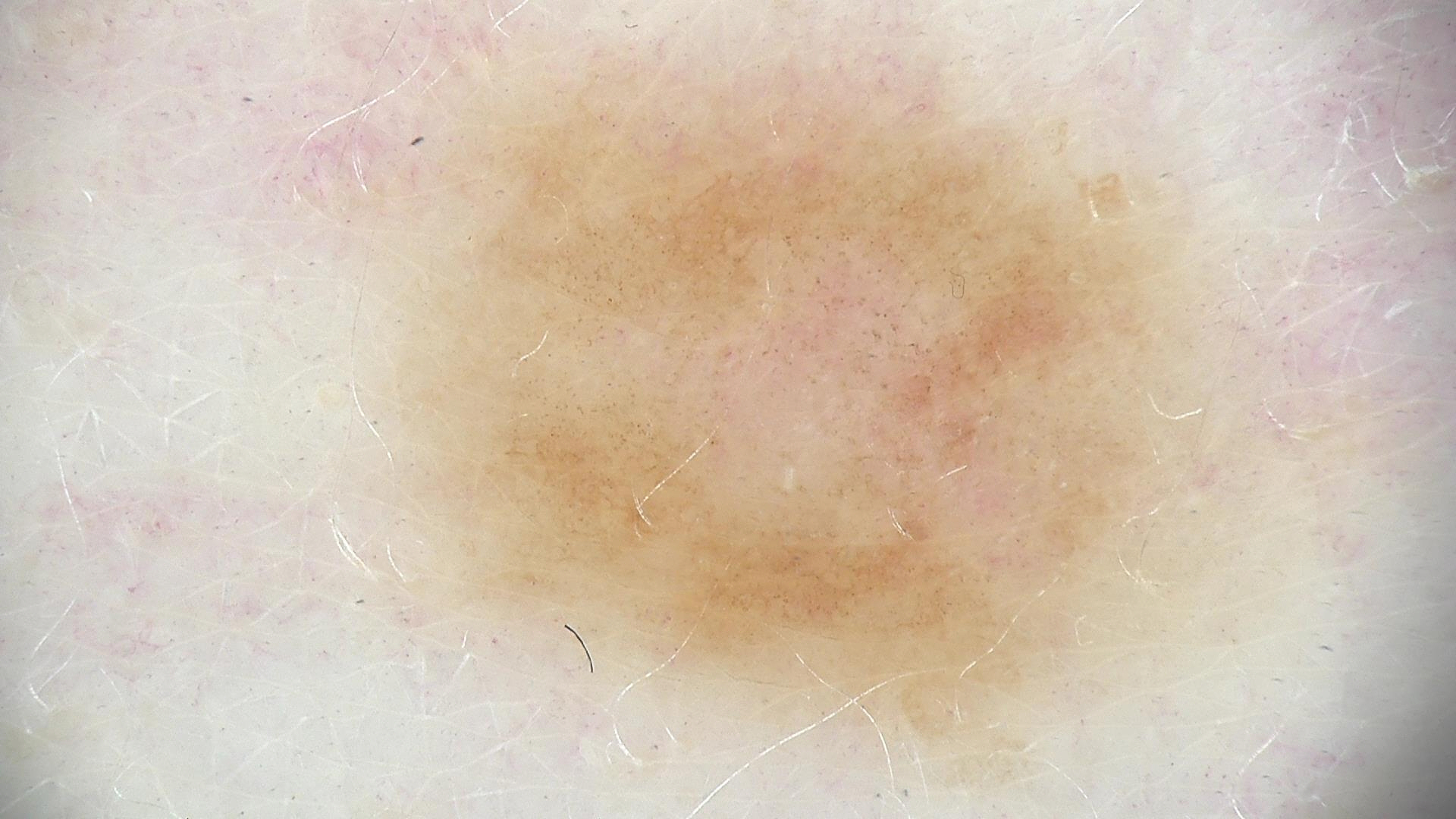modality=dermoscopy | class=dysplastic junctional nevus (expert consensus).